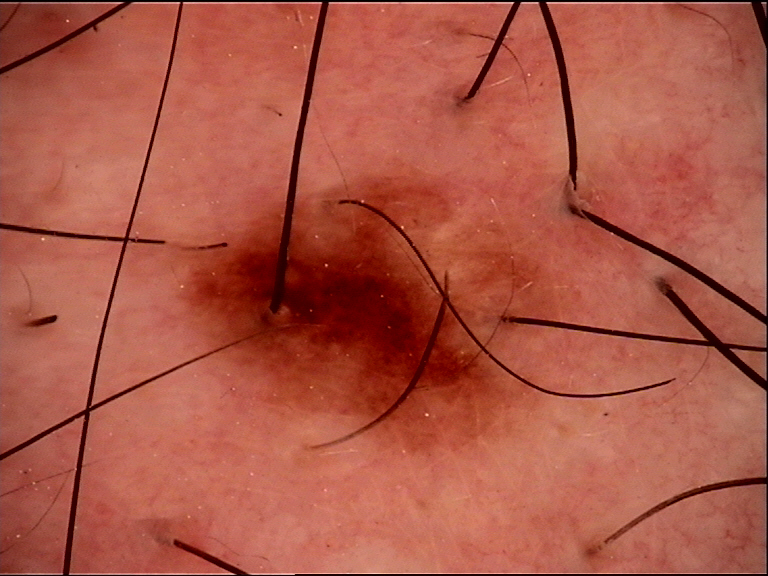Case:
The morphology is that of a banal lesion.
Impression:
Consistent with a compound nevus.